The patient is a female aged 18–29, the lesion involves the leg, this image was taken at an angle.
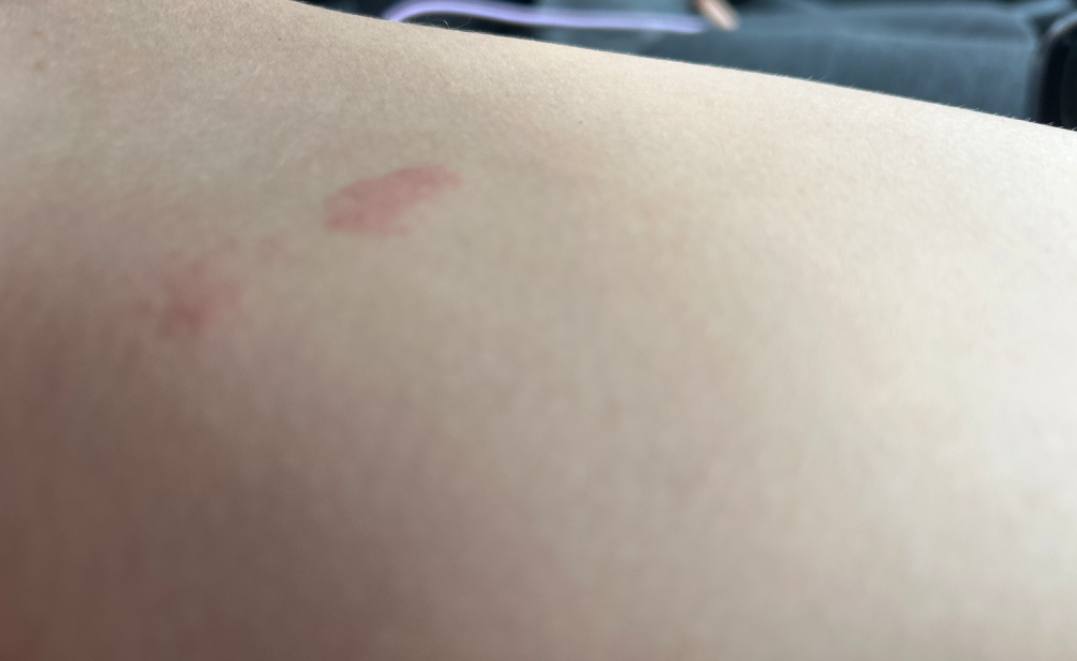assessment: unable to determine, onset: less than one week.